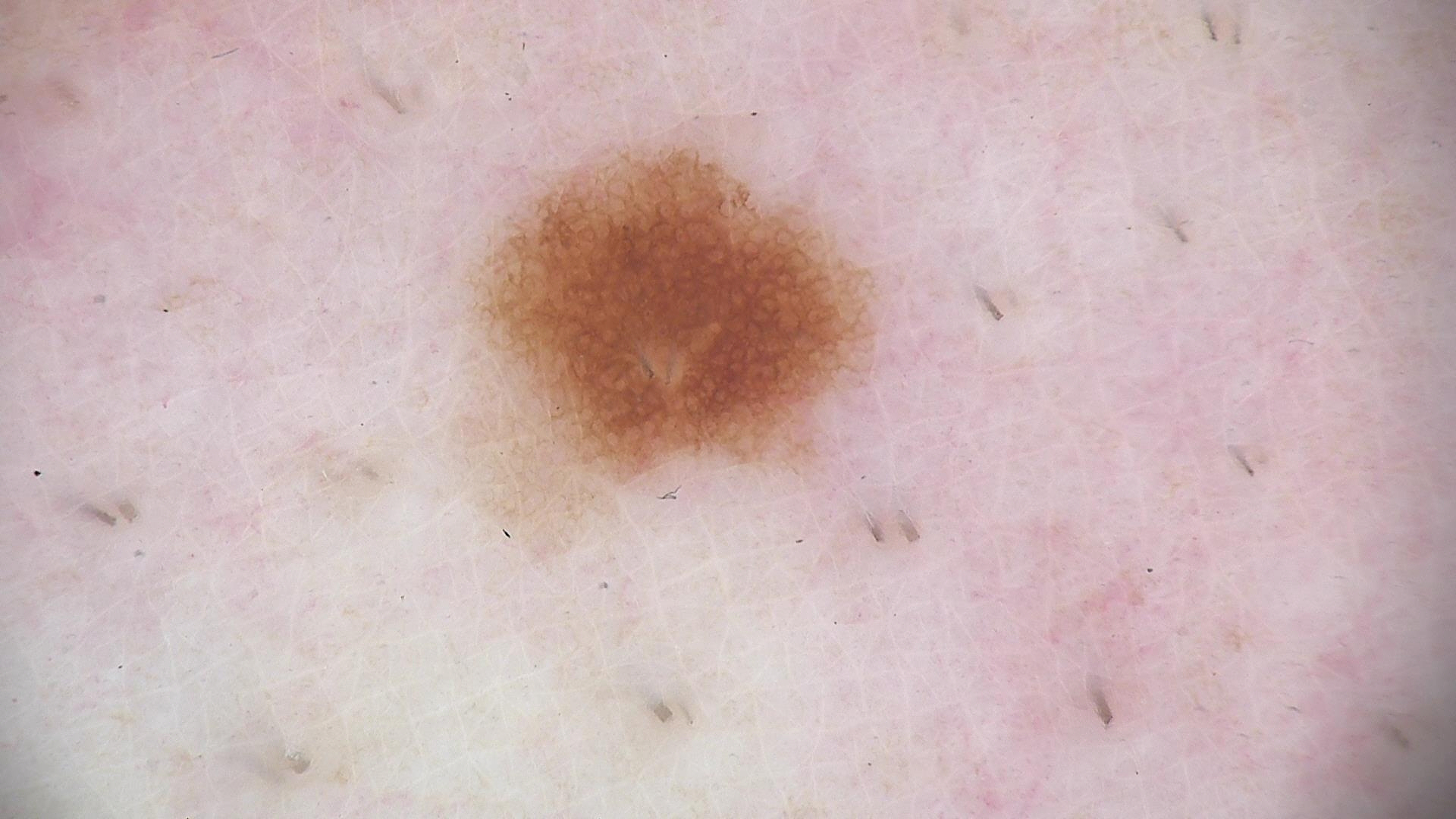Consistent with a dysplastic junctional nevus.